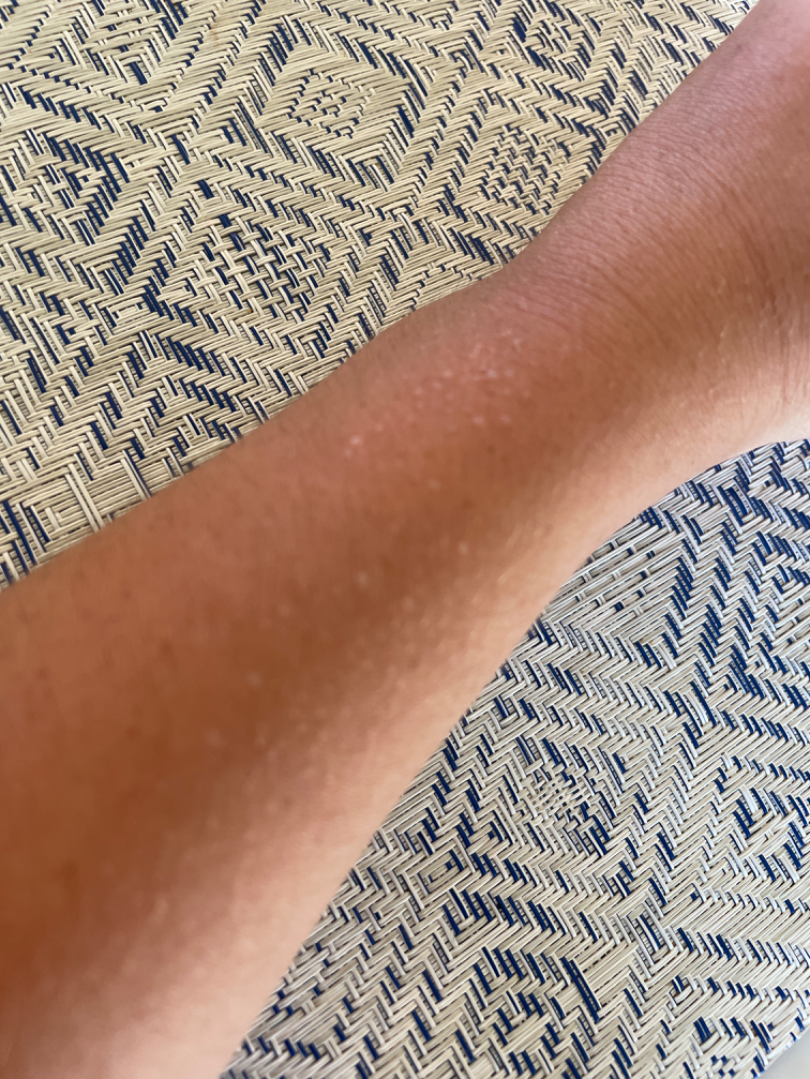Findings:
The skin condition could not be confidently assessed from this image.
Background:
The photograph is a close-up of the affected area.